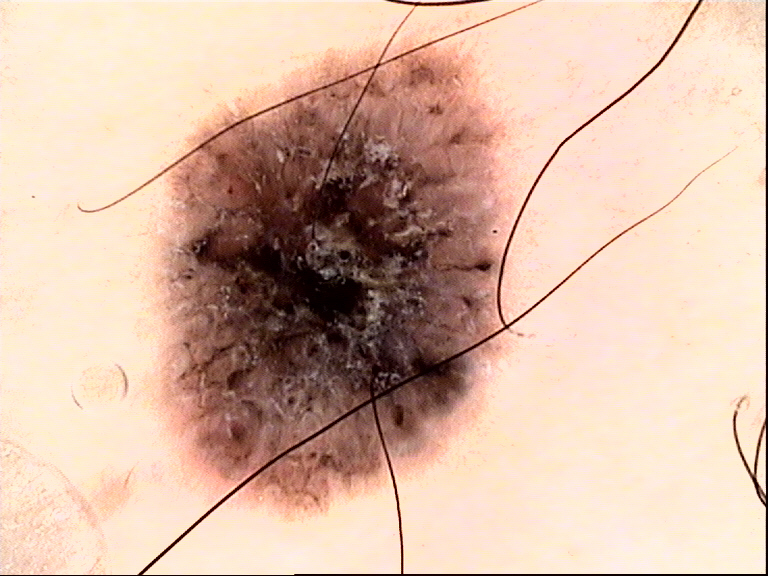Impression:
Diagnosed as a keratinocytic, benign lesion — a seborrheic keratosis.